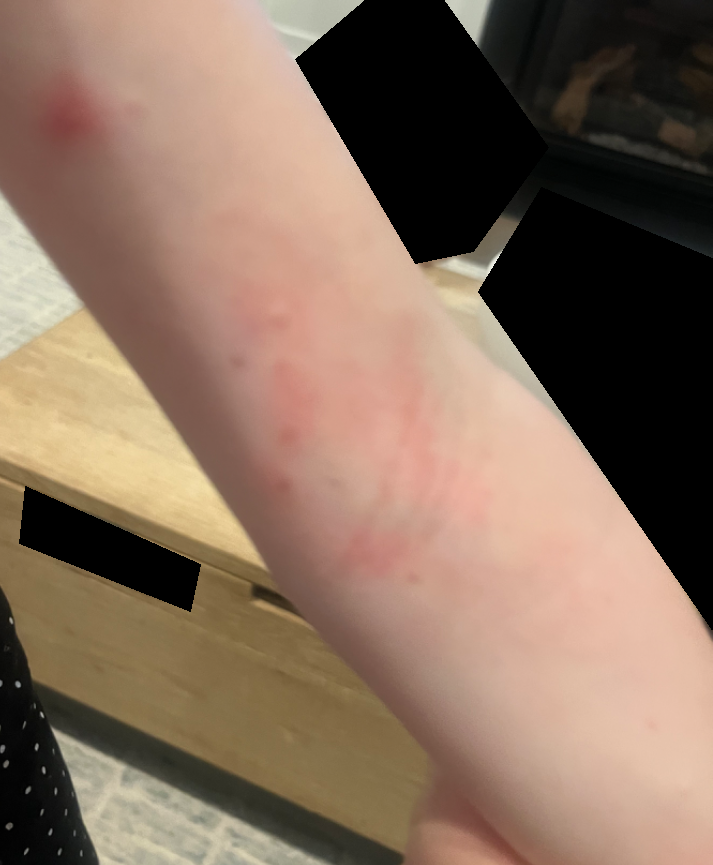History: The photograph is a close-up of the affected area. Impression: Most likely Eczema.